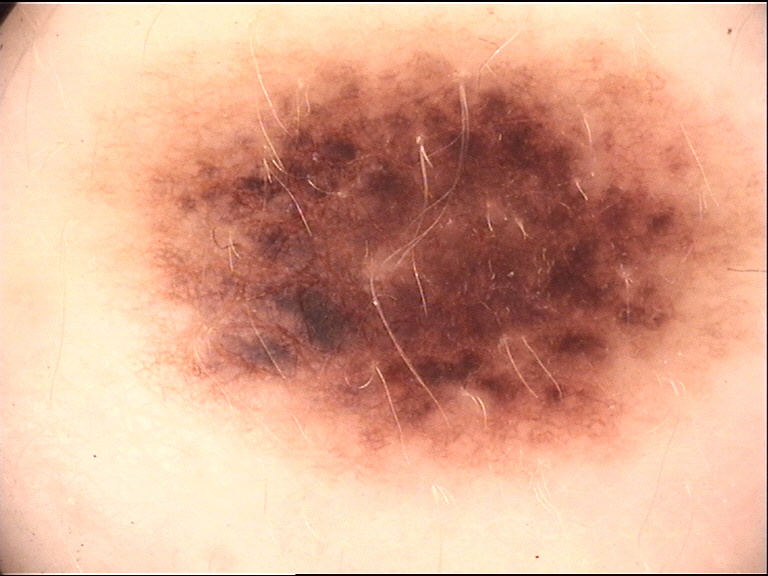{
  "image": "dermatoscopy",
  "diagnosis": {
    "name": "dysplastic junctional nevus",
    "code": "jd",
    "malignancy": "benign",
    "super_class": "melanocytic",
    "confirmation": "expert consensus"
  }
}